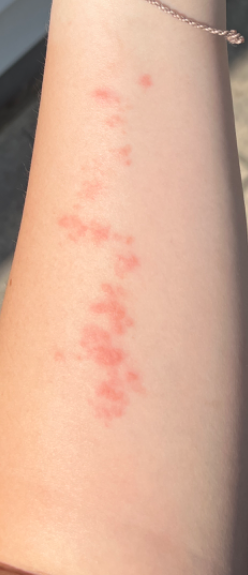| feature | finding |
|---|---|
| location | arm |
| contributor | female, age 18–29 |
| shot type | at a distance |
| impression | Insect Bite (considered); Allergic Contact Dermatitis (considered); Herpes Zoster (less likely) |